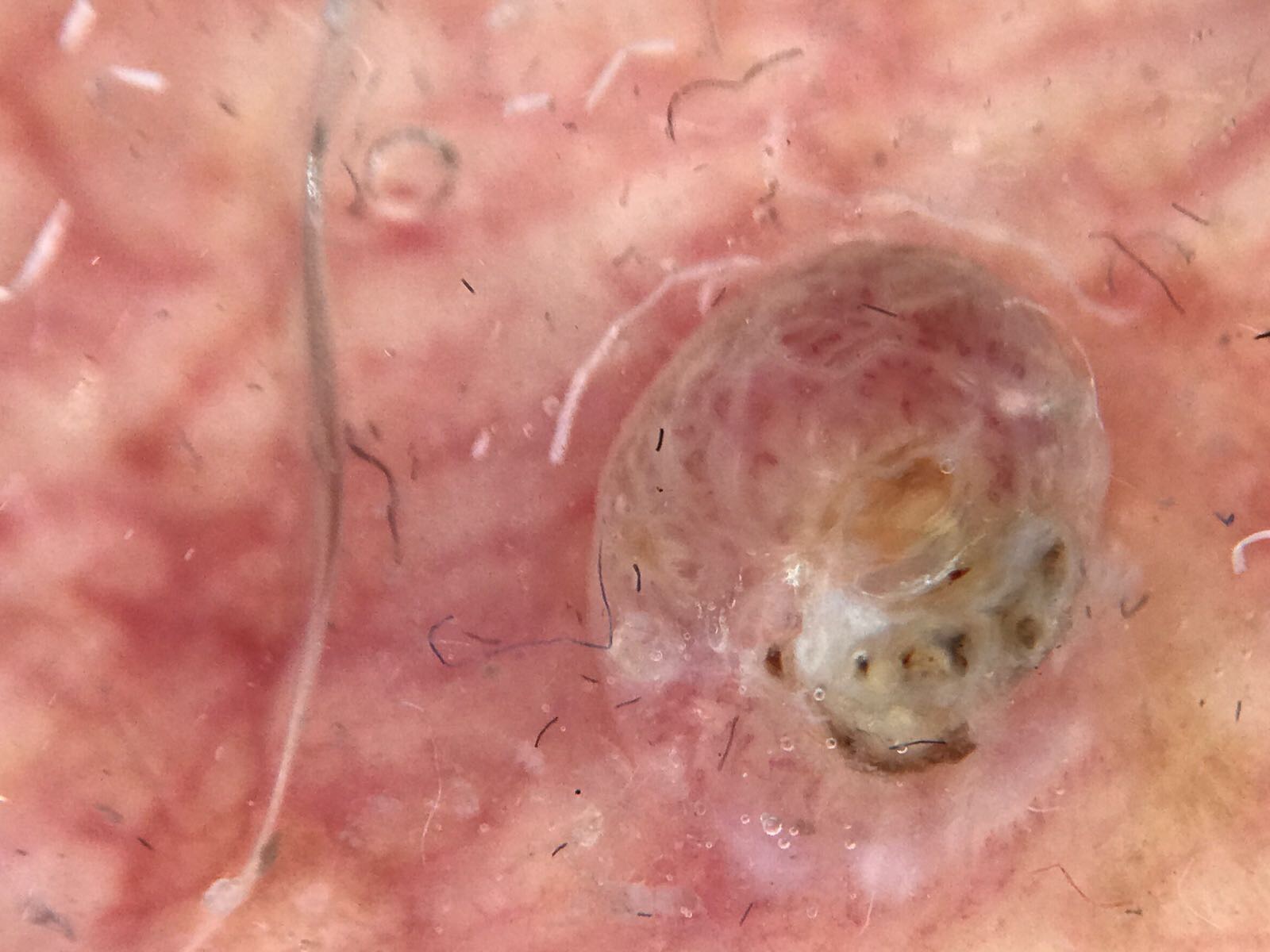Histopathology confirmed a squamous cell carcinoma.